A close-up photograph:
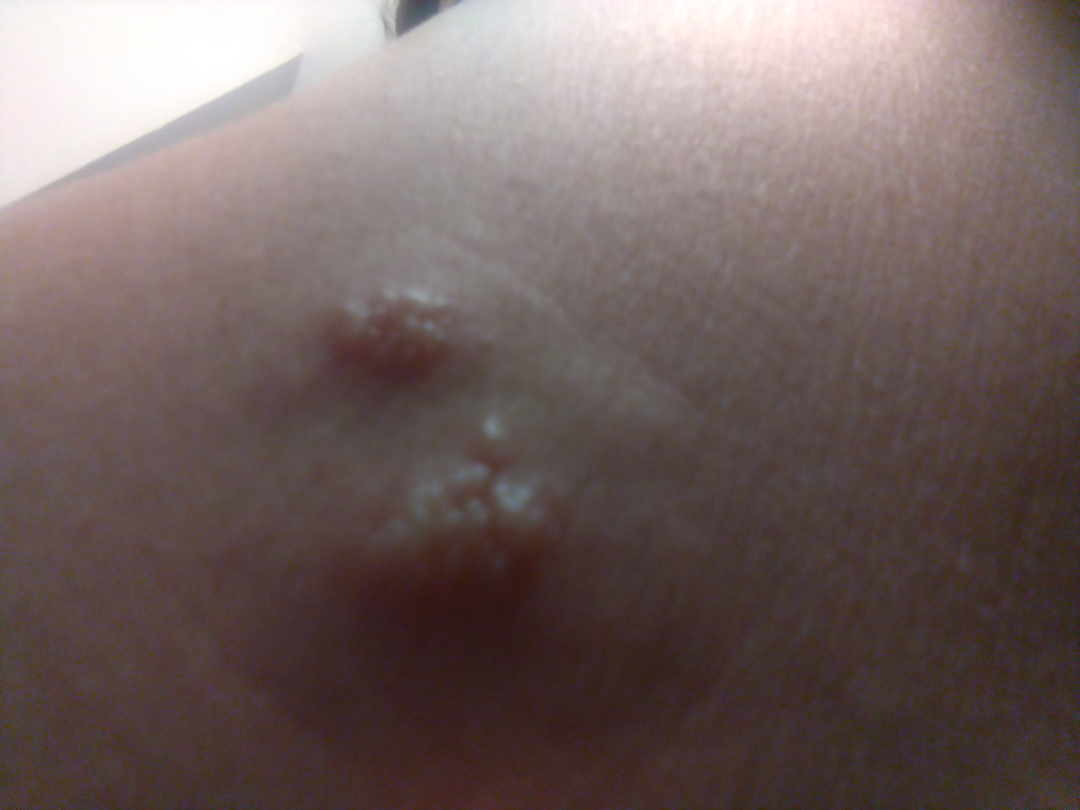The reviewing dermatologist was unable to assign a differential diagnosis from the image.
Fitzpatrick phototype III; non-clinician graders estimated Monk Skin Tone 2 or 3 (two reviewer pools).